A dermoscopic image of a skin lesion: 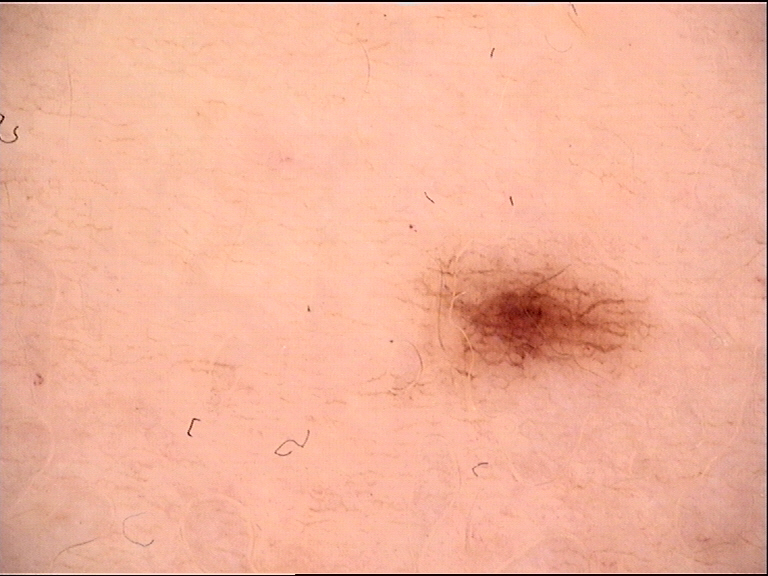Classified as a dysplastic junctional nevus.